The photo was captured at an angle · the patient is 30–39, male · located on the arm, leg and back of the torso — 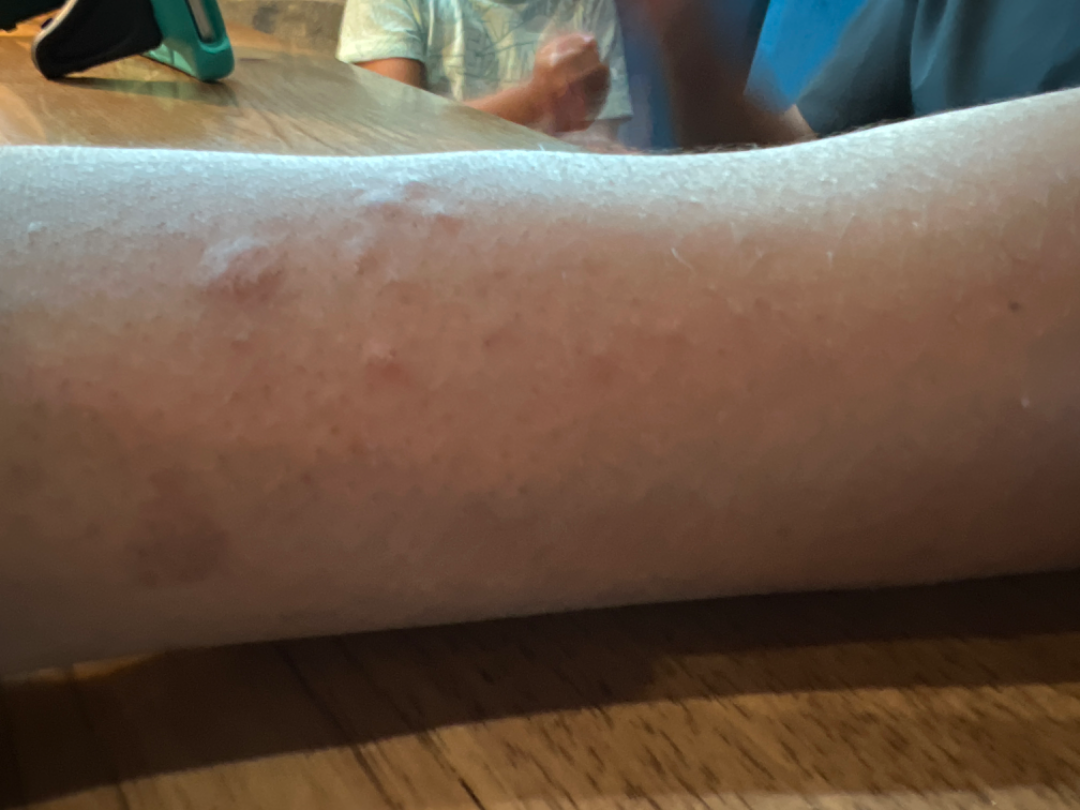Q: Could the case be diagnosed?
A: could not be assessed